The patient reported no systemic symptoms. An image taken at a distance. Female subject, age 40–49. Reported lesion symptoms include itching. The patient considered this a rash. The back of the hand, front of the torso, leg and head or neck are involved. The contributor reports the lesion is raised or bumpy and rough or flaky. Skin tone: Fitzpatrick phototype II; non-clinician graders estimated MST 3 (US pool) or 2 (India pool). The contributor reports the condition has been present for less than one week: 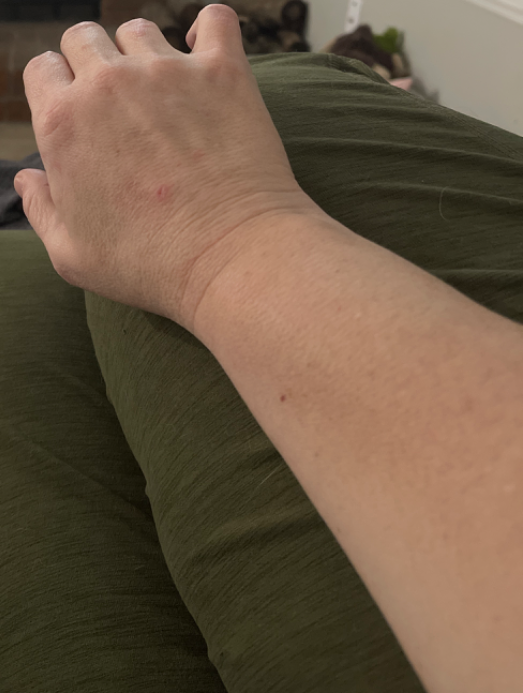The primary impression is Eczema.